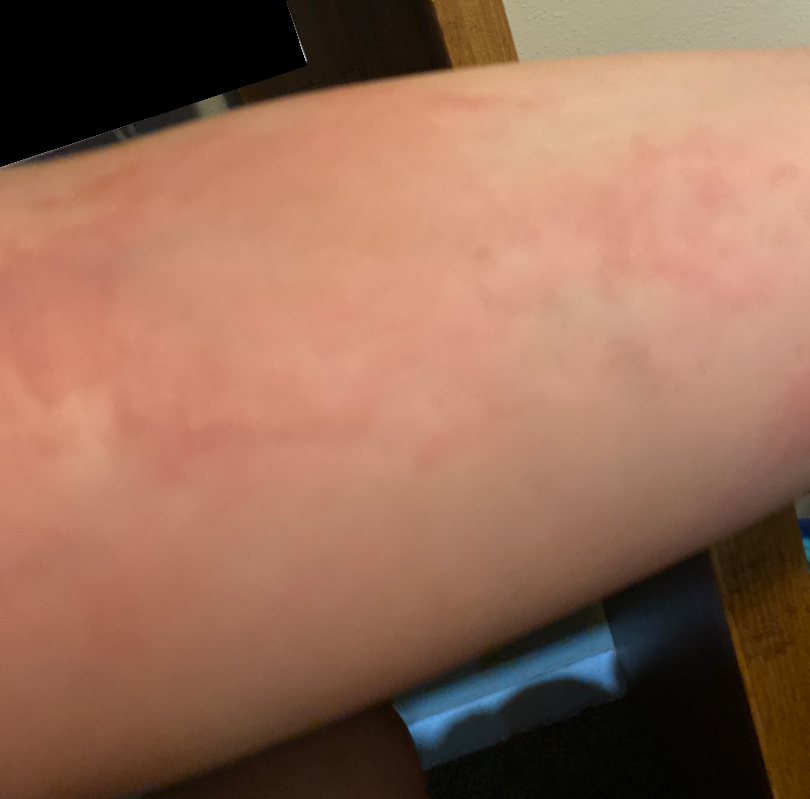Background: The arm is involved. Texture is reported as raised or bumpy. Self-categorized by the patient as a rash. The patient indicates enlargement, itching and bothersome appearance. The patient is female. Present for less than one week. An image taken at an angle. Findings: The favored diagnosis is Eczema; with consideration of Urticaria; an alternative is Psoriasis.